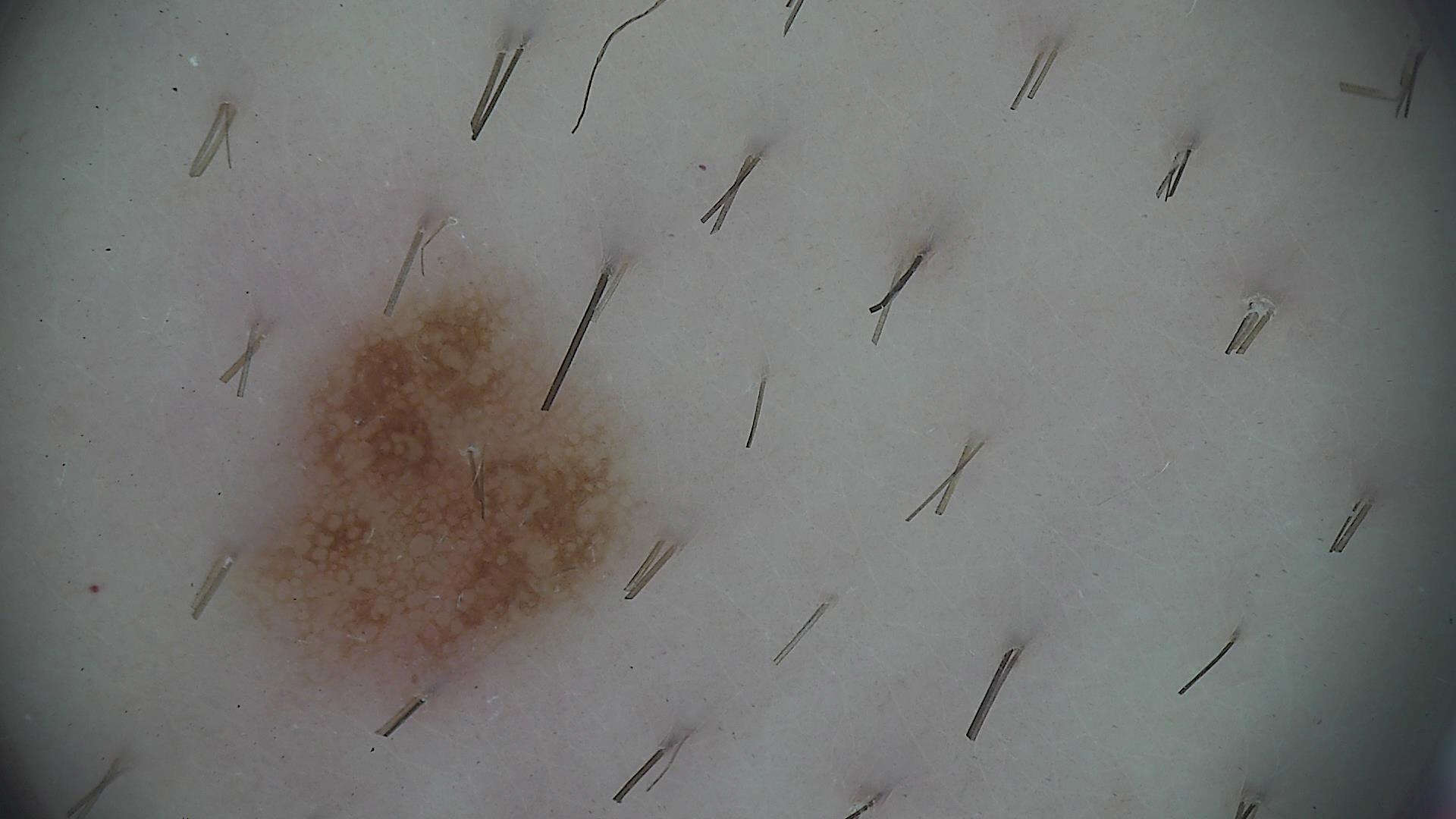| field | value |
|---|---|
| imaging | dermatoscopy |
| diagnosis | dysplastic junctional nevus (expert consensus) |